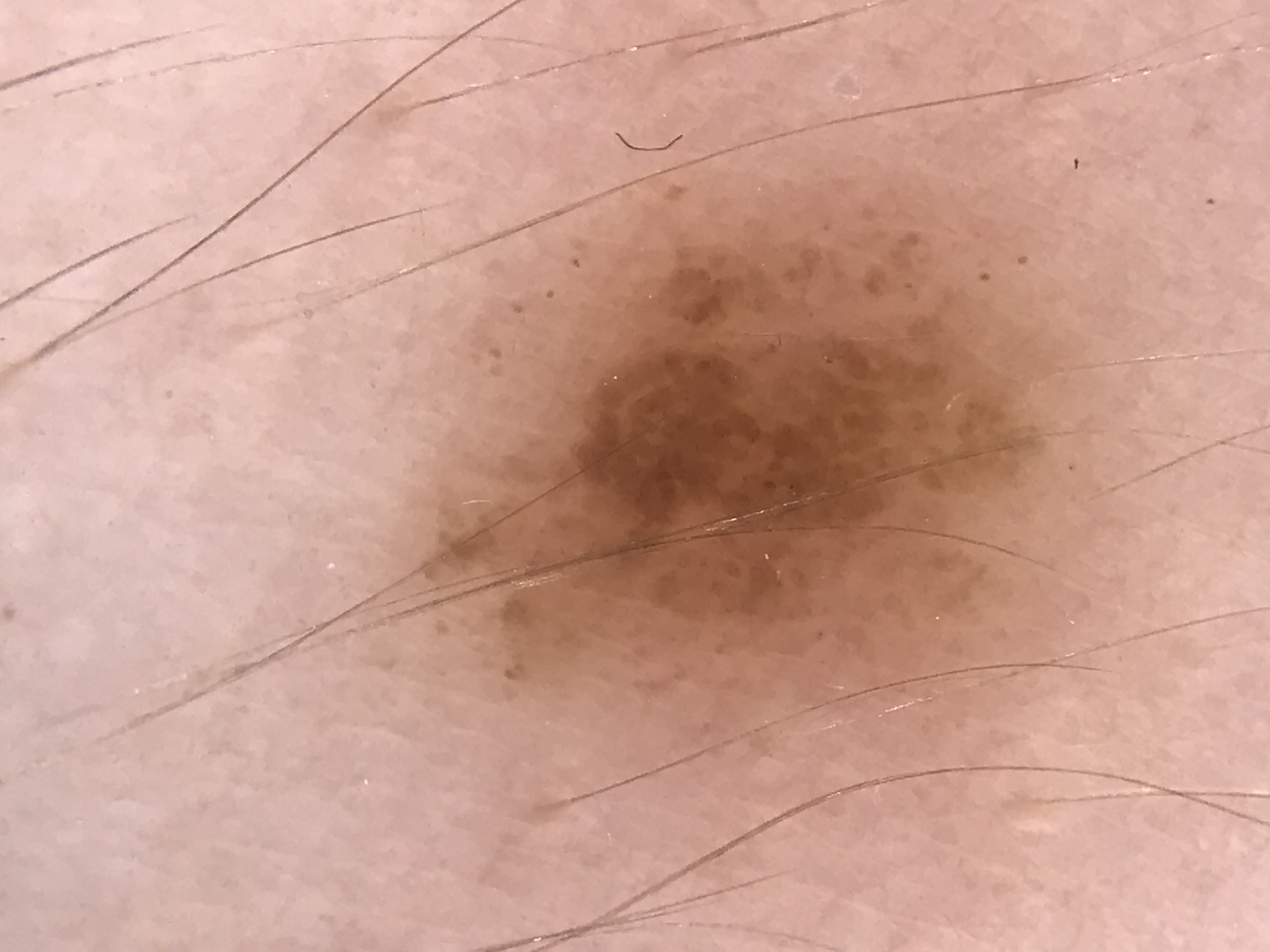image type: dermoscopy
diagnosis: dysplastic compound nevus (expert consensus)